The lesion involves the arm. The photograph is a close-up of the affected area — 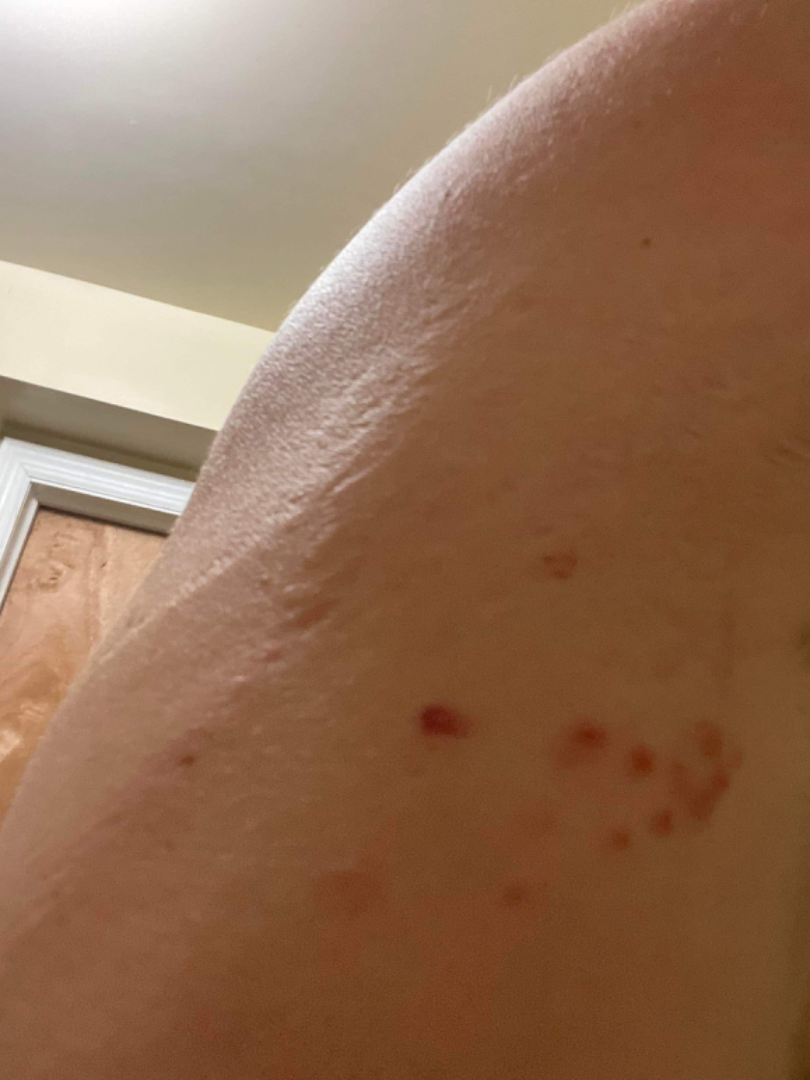No differential diagnosis could be assigned on photographic review.